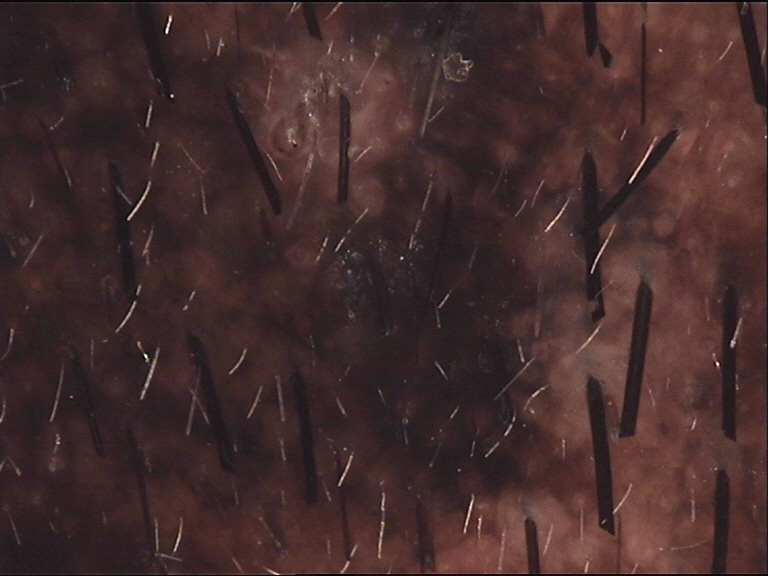Labeled as a congenital compound nevus.